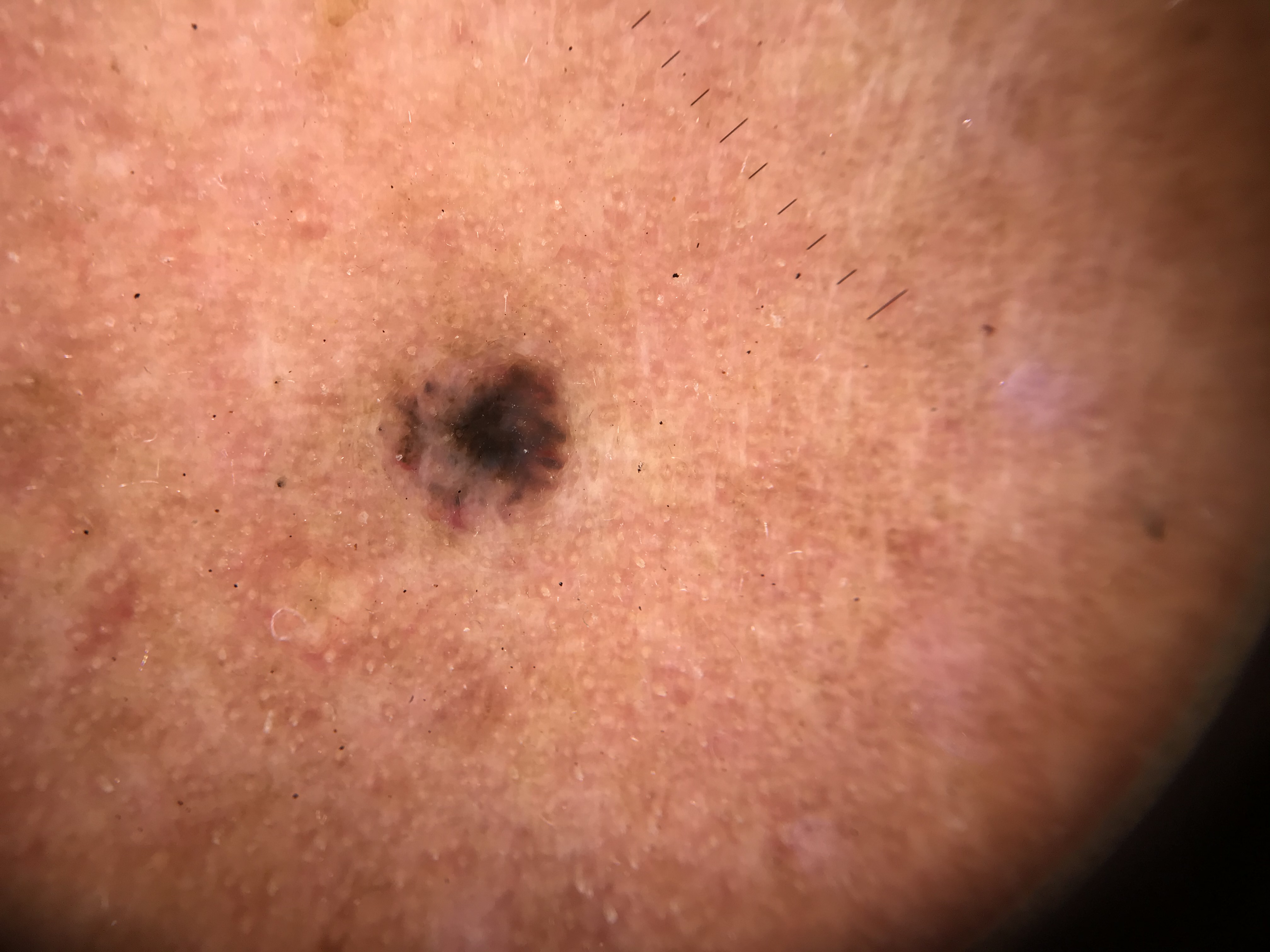image = dermatoscopy | subtype = keratinocytic | class = basal cell carcinoma (biopsy-proven).